Texture is reported as raised or bumpy and rough or flaky; the patient indicates the condition has been present for more than one year; the subject is a female aged 30–39; this image was taken at a distance; the patient considered this acne:
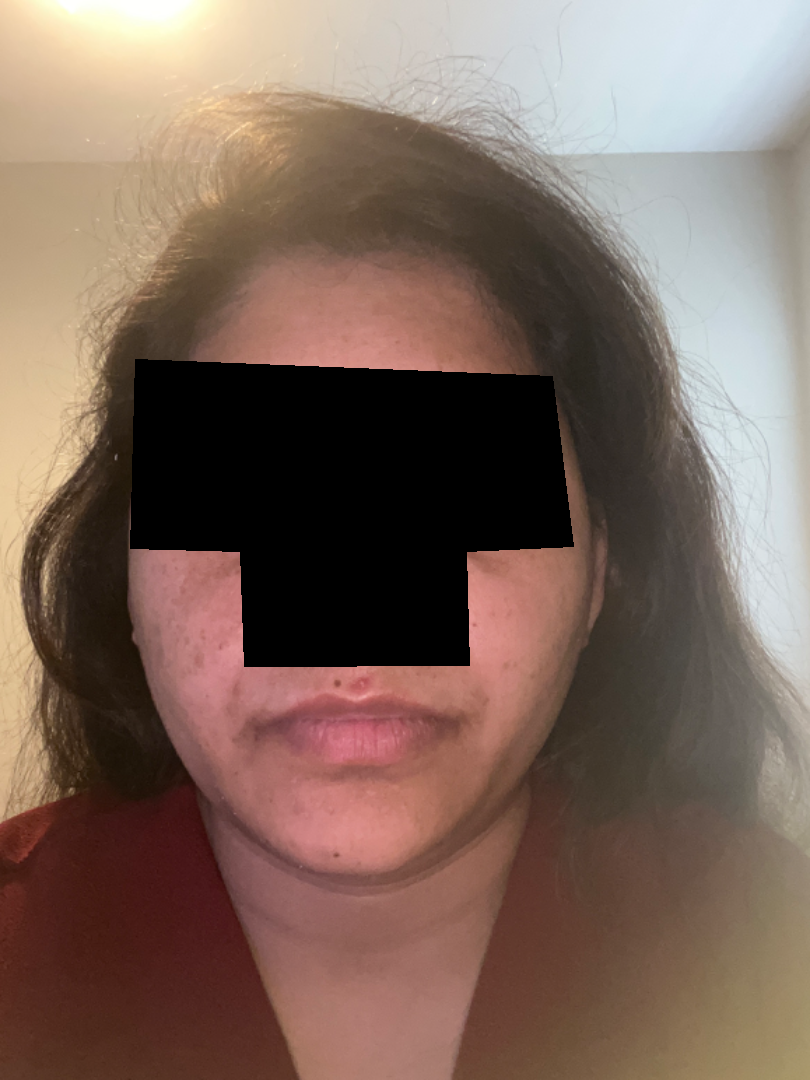| key | value |
|---|---|
| dermatologist impression | the favored diagnosis is Acne |